A male subject, approximately 40 years of age. A dermoscopic view of a skin lesion: 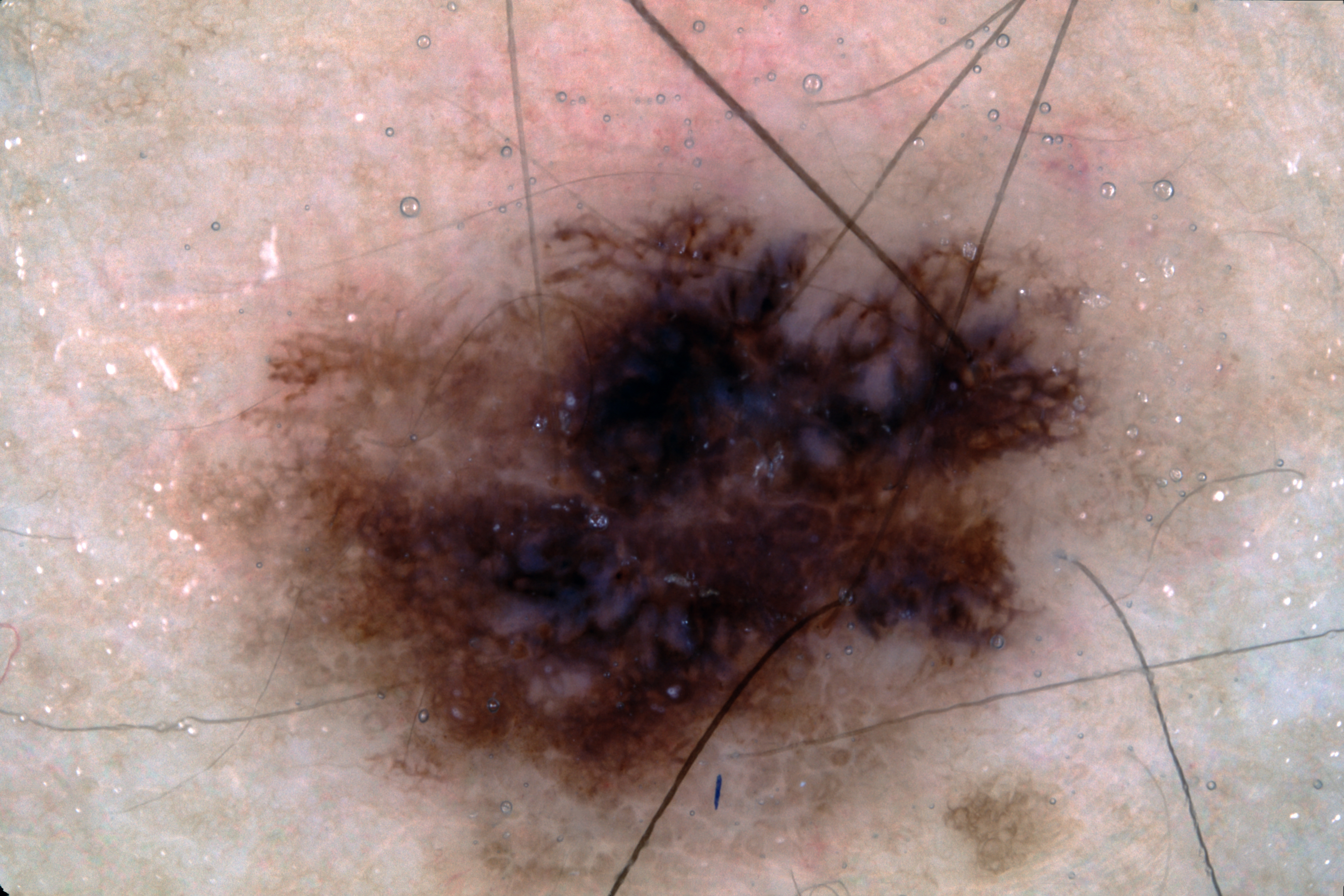The dermoscopic pattern shows pigment network and negative network; no milia-like cysts or streaks. The lesion occupies the region 199 196 1102 826. The lesion covers approximately 34% of the dermoscopic field. Histopathological examination showed a melanoma, a skin cancer.